This image was taken at a distance · non-clinician graders estimated Monk skin tone scale 3 or 4:
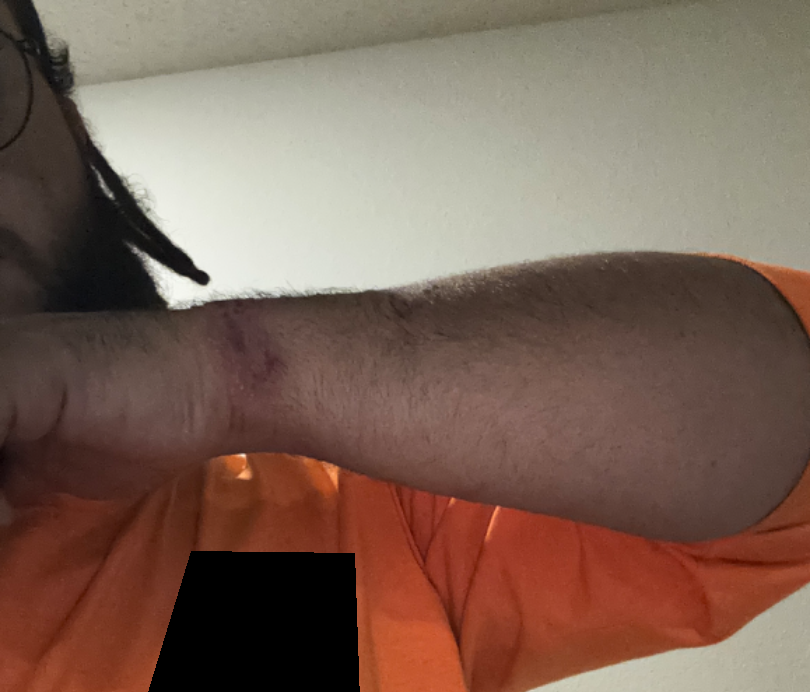The leading impression is Allergic Contact Dermatitis; also raised was Irritant Contact Dermatitis.